Dermoscopy of a skin lesion.
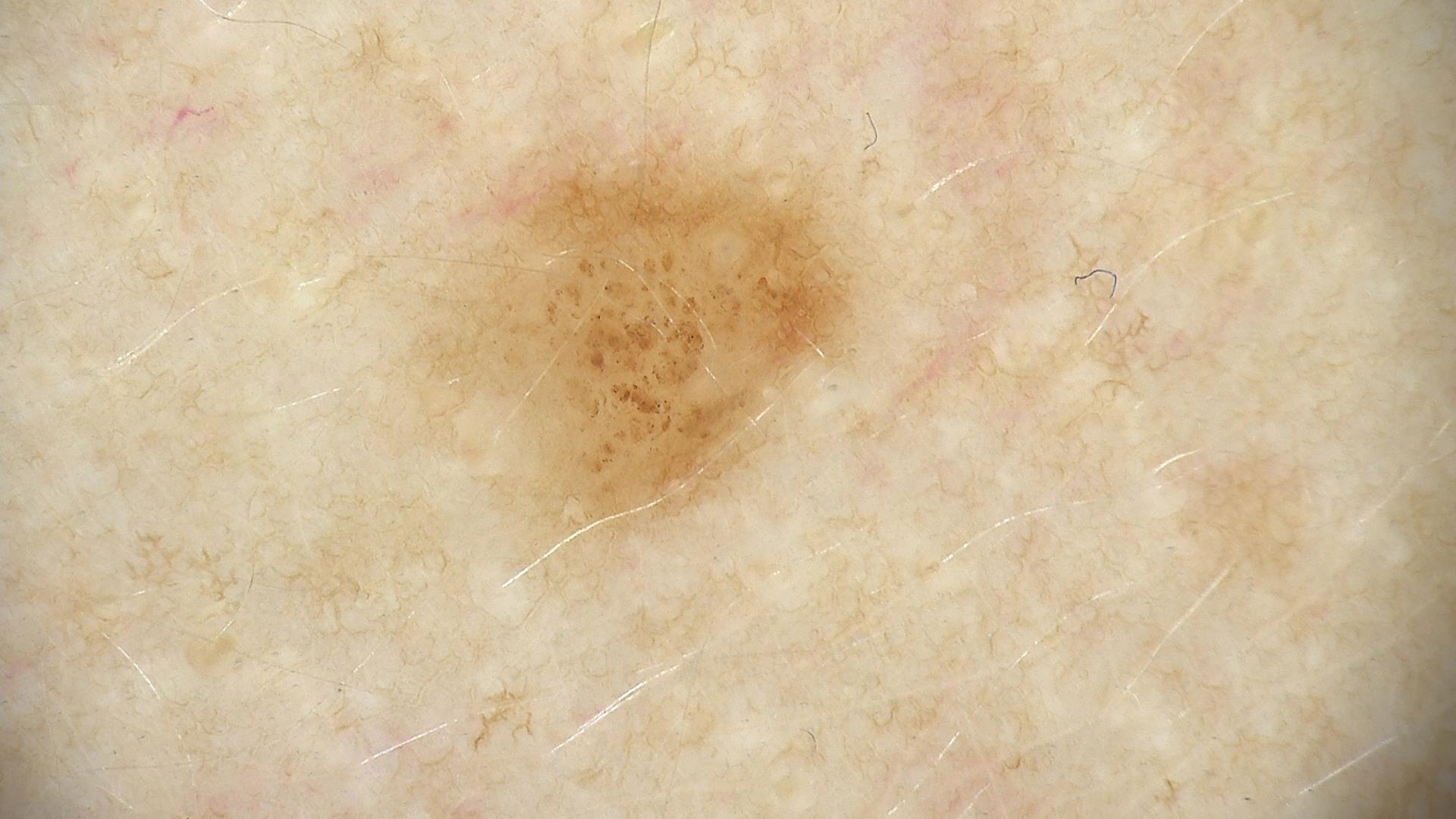Conclusion:
Consistent with a dysplastic junctional nevus.